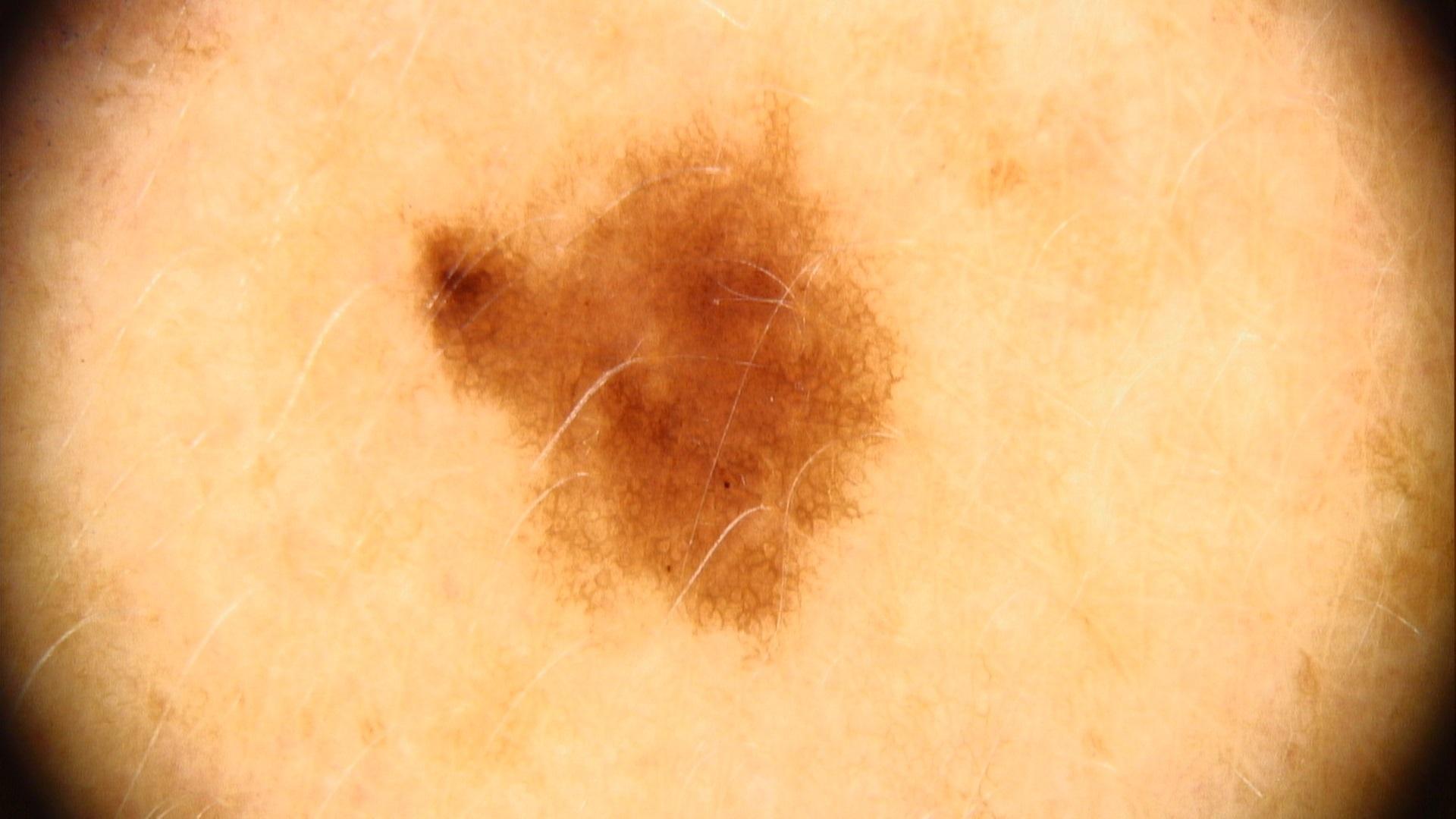Summary: The lesion is on the trunk. Assessment: Consistent with a benign, melanocytic lesion — a nevus.